The photograph is a close-up of the affected area, the affected area is the head or neck: 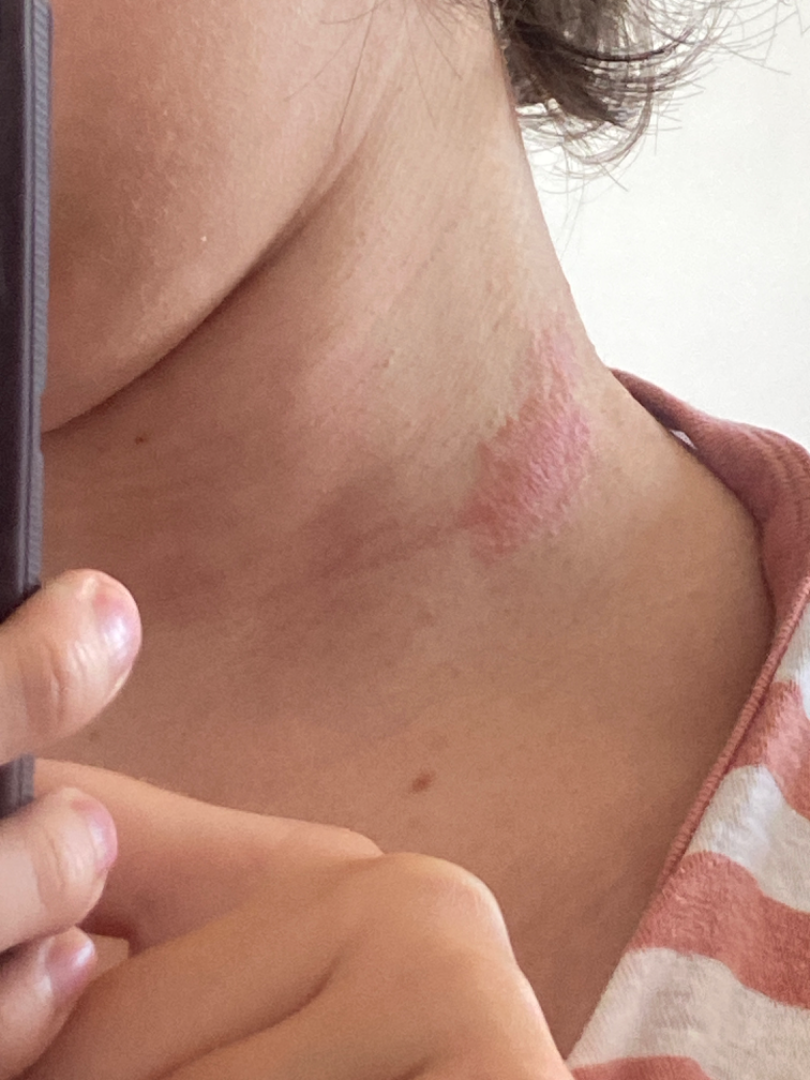On remote dermatologist review: most consistent with Irritant Contact Dermatitis; also consider Allergic Contact Dermatitis.